The patient reports a personal history of skin cancer and a personal history of cancer; a female patient aged 60; referred with a clinical suspicion of basal cell carcinoma; the patient describes having few moles overall.
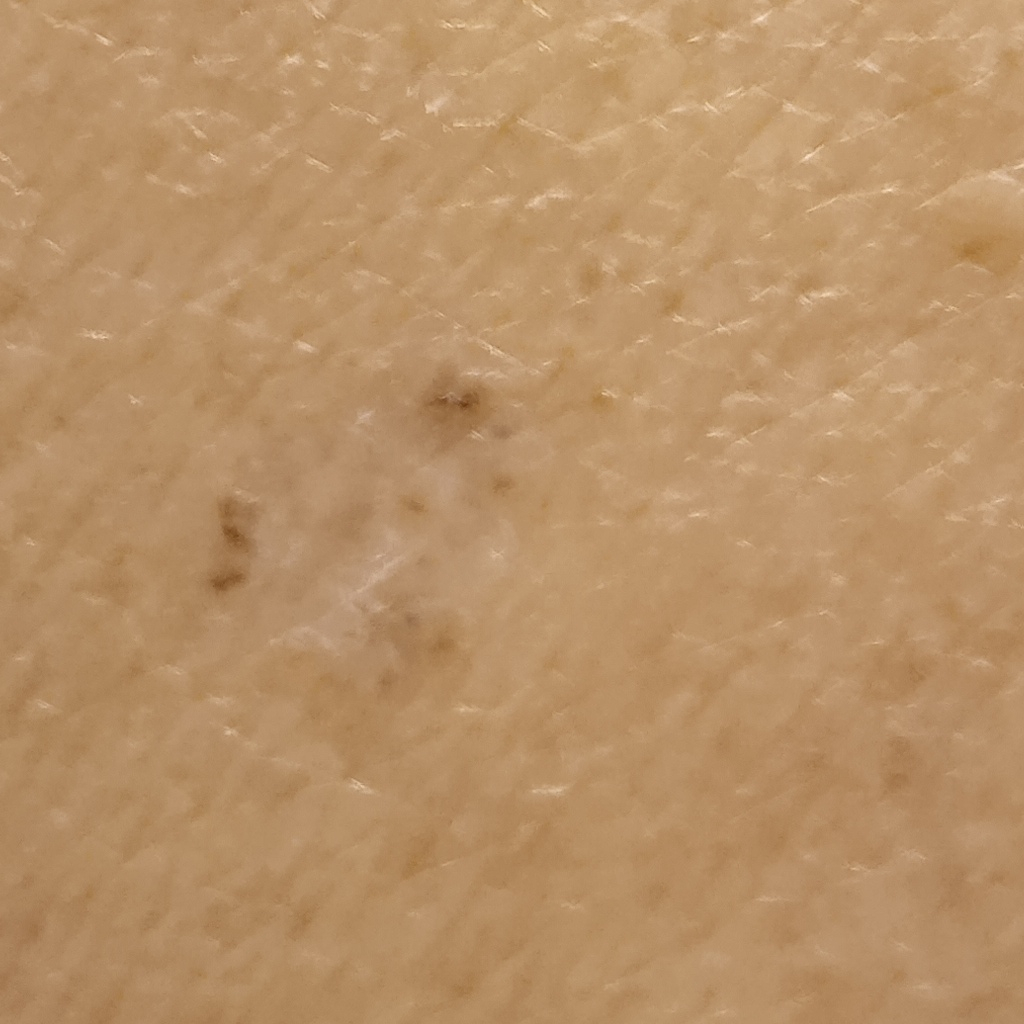site = the back; diagnosis = basal cell carcinoma (dermatologist consensus).